The affected area is the arm, front of the torso and leg. The patient described the issue as a rash. The condition has been present for about one day. The lesion is described as raised or bumpy. Close-up view. The contributor notes burning, enlargement and itching. Female patient, age 40–49: 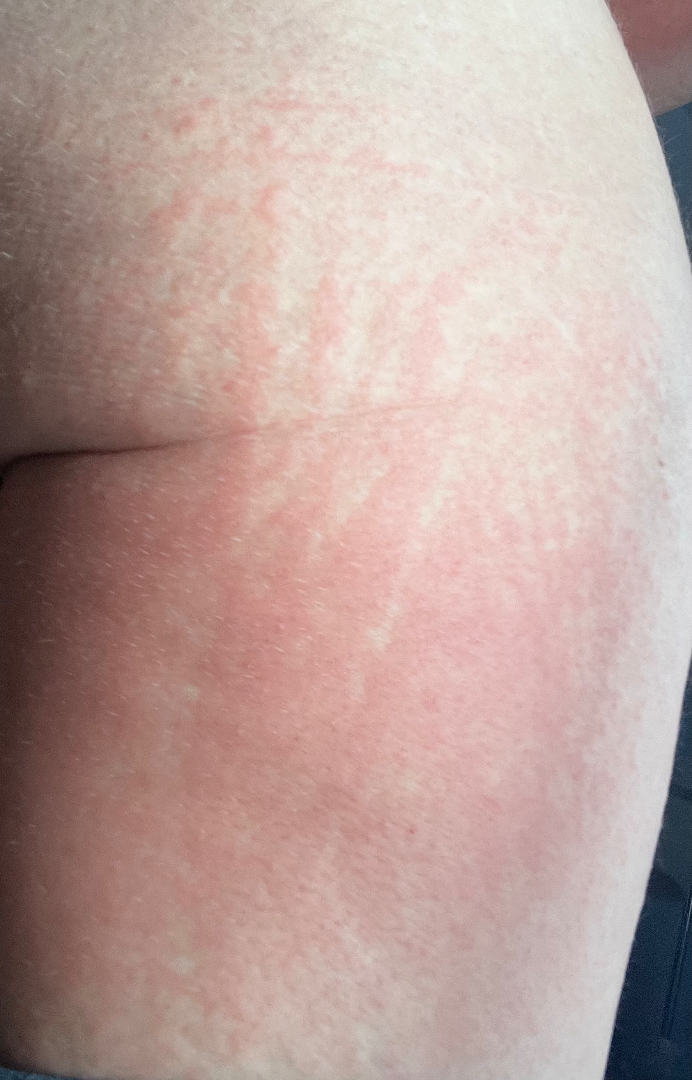<case>
  <differential>
    <leading>Urticaria</leading>
  </differential>
</case>